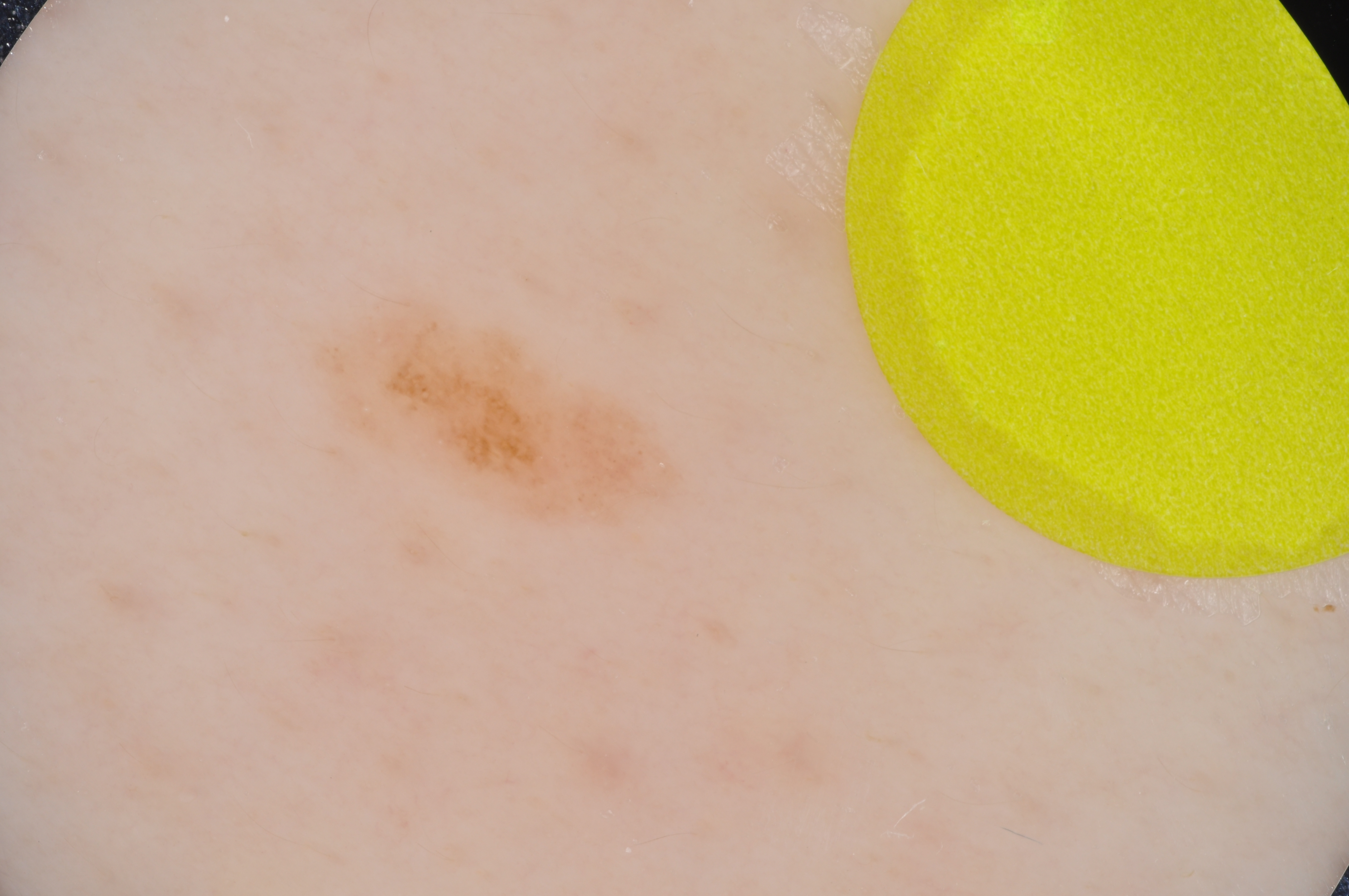Case summary: A male subject, about 15 years old. A dermoscopy image of a single skin lesion. Dermoscopically, the lesion shows no streaks, negative network, milia-like cysts, globules, or pigment network. A small lesion occupying a minor part of the field. The lesion's extent is [311,297,697,533]. Impression: Expert review diagnosed this as a melanocytic nevus, a benign skin lesion.